This image was taken at a distance, the subject is a female aged 50–59, the affected area is the arm and palm.
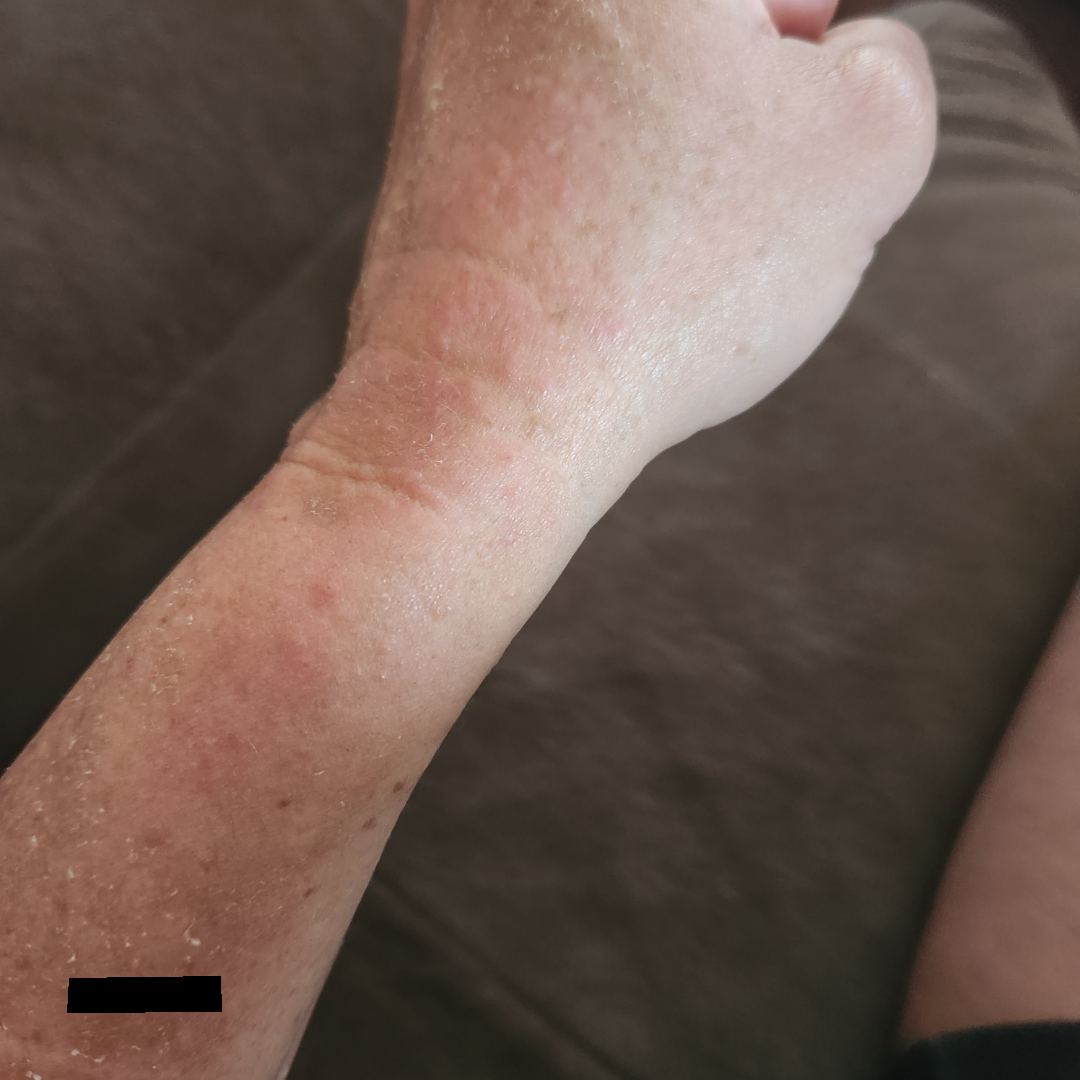The case was difficult to assess from the available photograph.